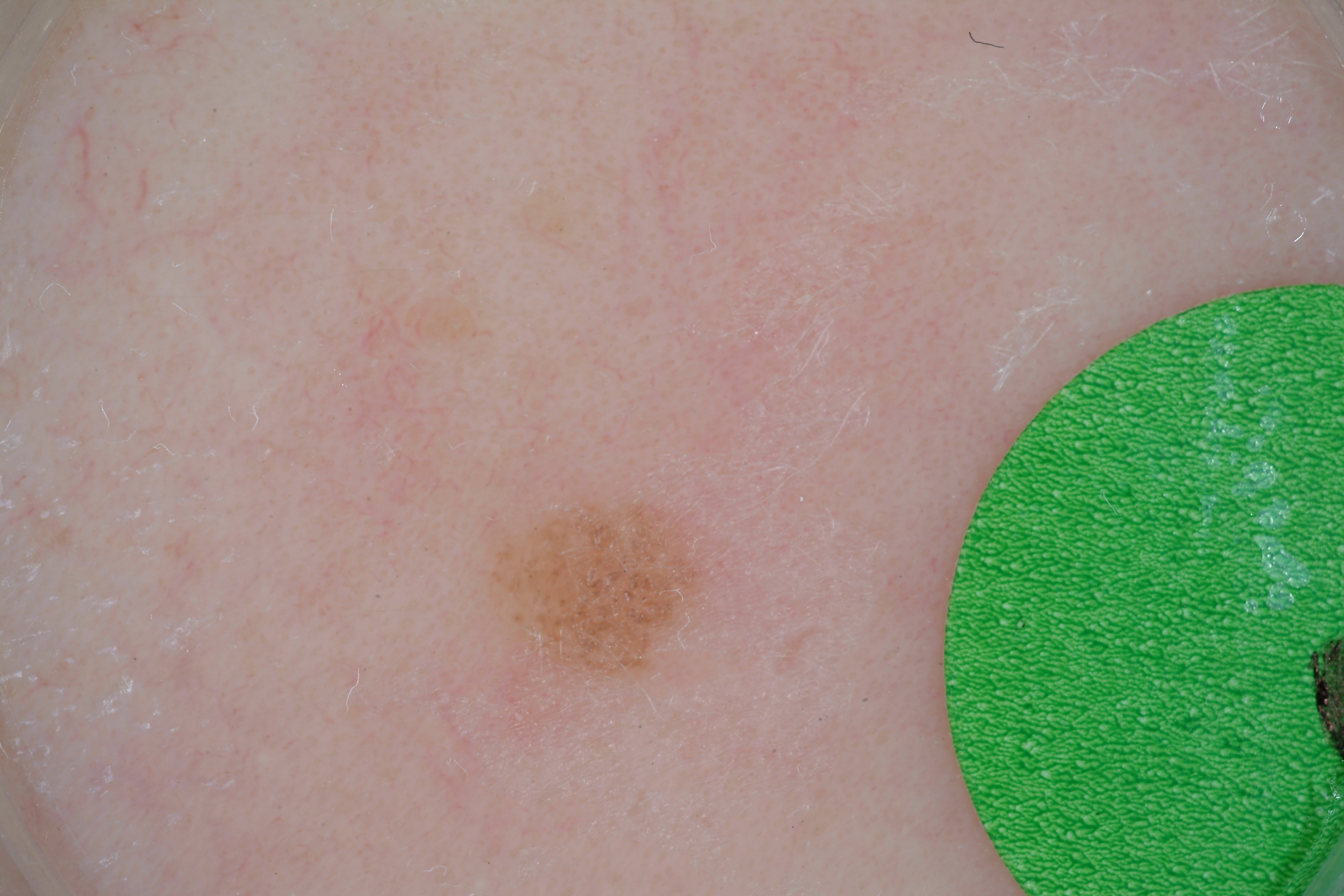image type: dermoscopy; subject: male, about 10 years old; dermoscopic features not present: streaks, milia-like cysts, negative network, and pigment network; location: 479, 492, 702, 690; lesion size: ~3% of the field; impression: a melanocytic nevus, a benign lesion.